A clinical close-up photograph of a skin lesion; a female subject in their mid-70s.
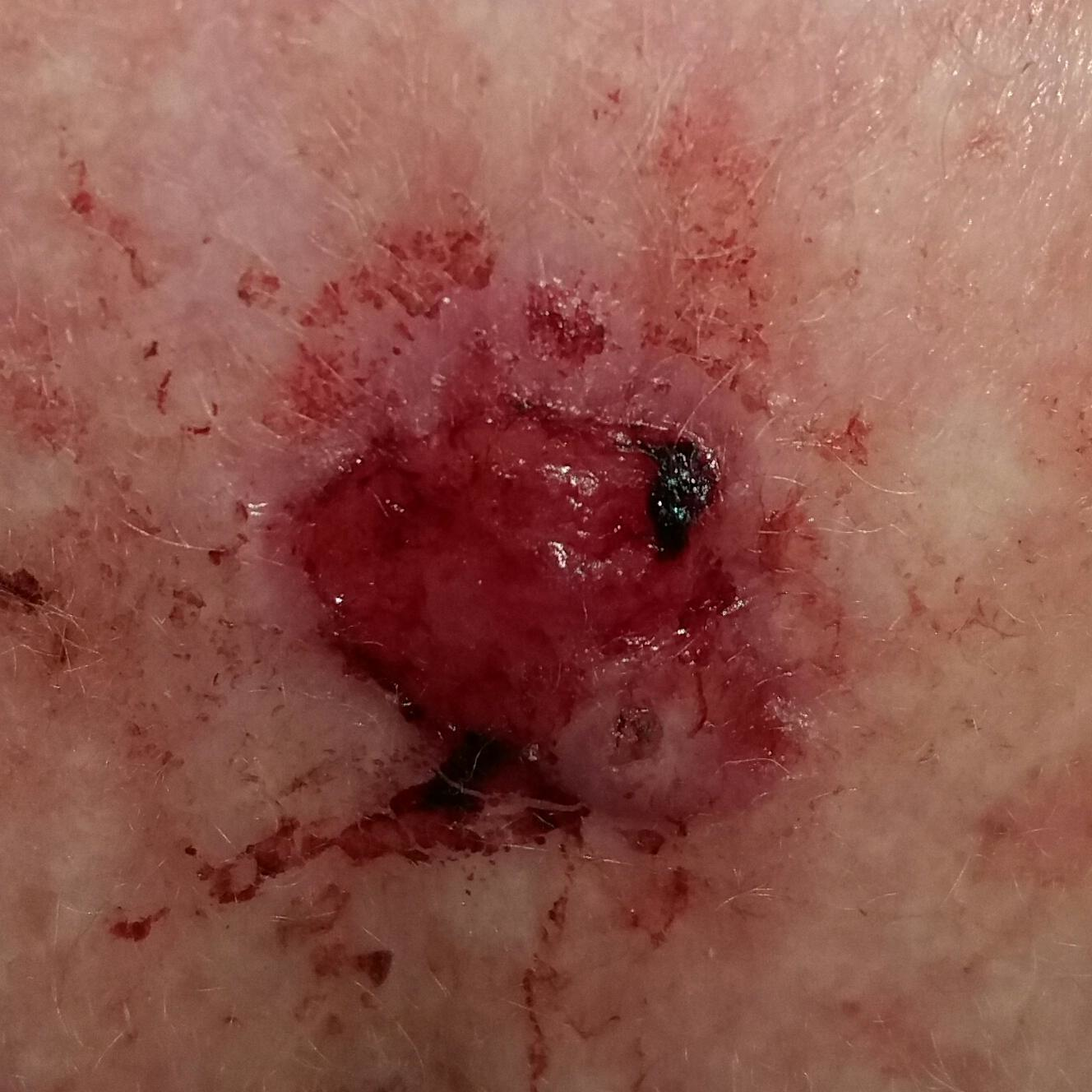reported symptoms: itching, elevation, bleeding, growth
diagnostic label: basal cell carcinoma (biopsy-proven)